The top or side of the foot, leg and palm are involved; the photograph was taken at a distance.
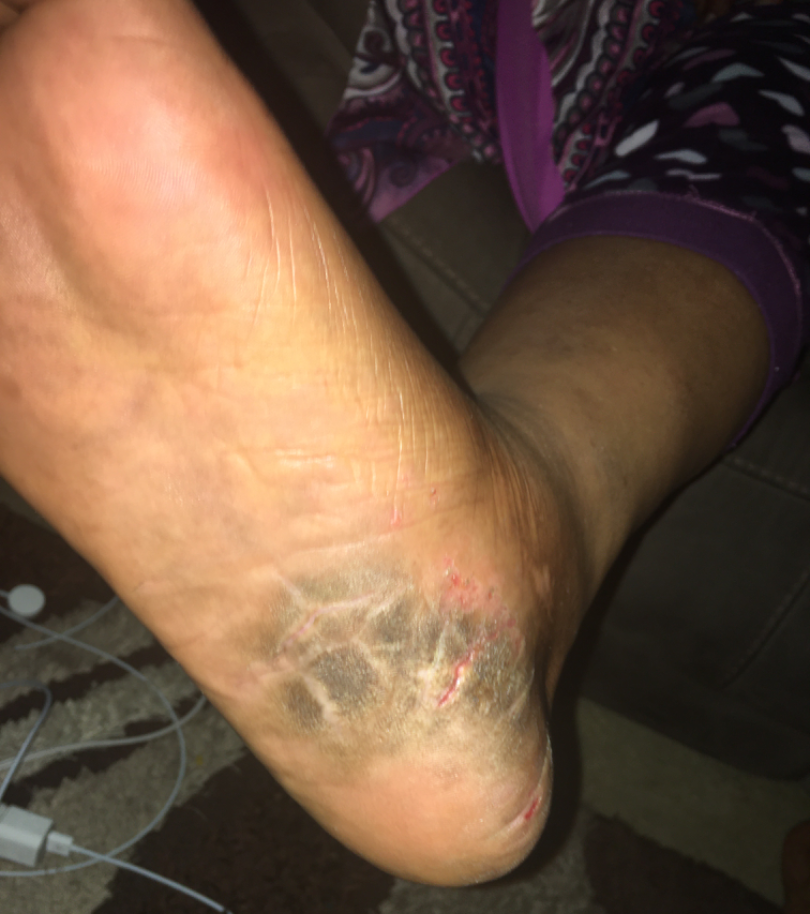| key | value |
|---|---|
| assessment | indeterminate |
| surface texture | rough or flaky |
| patient-reported symptoms | enlargement, pain, bothersome appearance, itching and darkening |
| history | more than one year |